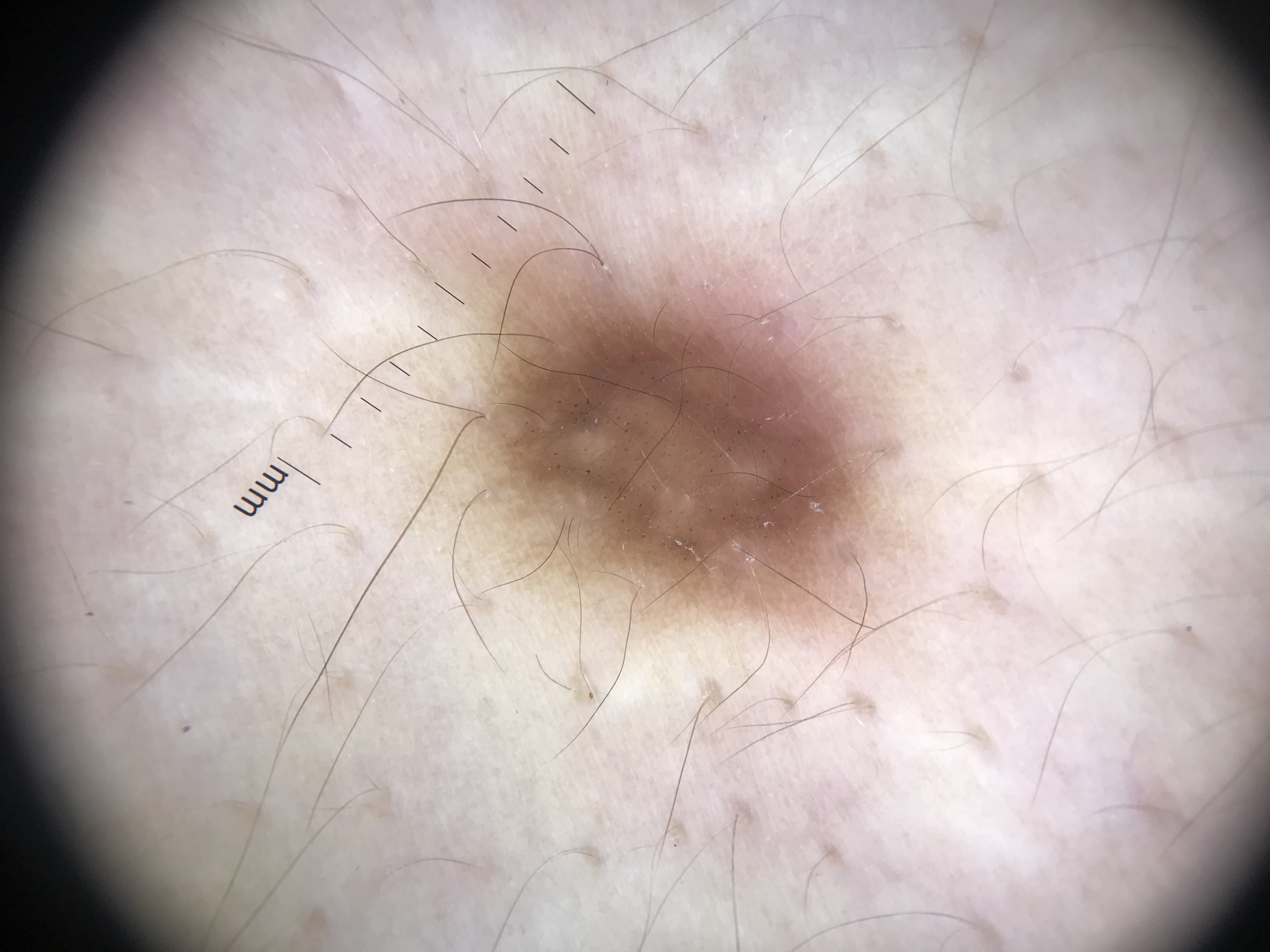Diagnosed as a dermatofibroma.